Reported duration is one to four weeks. Located on the head or neck. Self-categorized by the patient as skin that appeared healthy to them. Fitzpatrick phototype III; lay reviewers estimated Monk skin tone scale 3–4. The lesion is described as raised or bumpy. The subject is male. This is a close-up image:
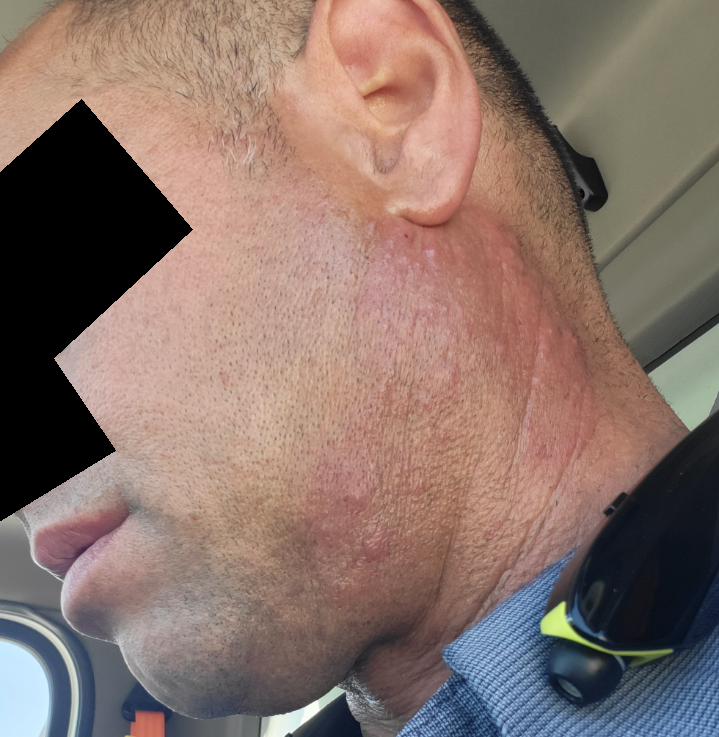Most consistent with Tinea; a more distant consideration is Impetigo; less likely is Allergic Contact Dermatitis; less probable is Acne; lower on the differential is Leprosy.